A dermoscopic view of a skin lesion, a male subject in their 70s.
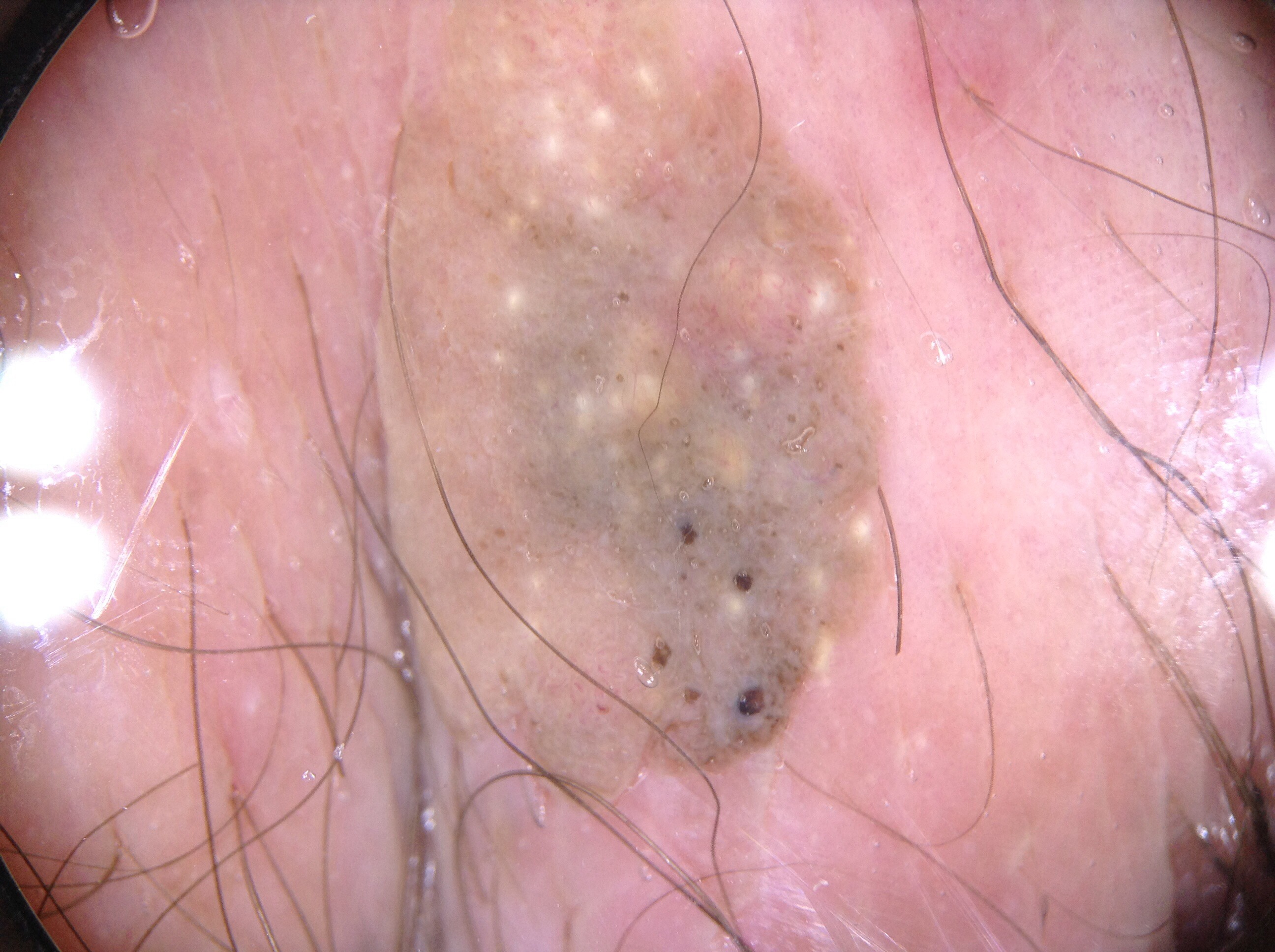Findings:
A prominent lesion filling much of the field. Dermoscopic examination shows milia-like cysts, with no streaks, pigment network, or negative network. In (x1, y1, x2, y2) order, the visible lesion spans bbox=[365, 2, 909, 812].
Conclusion:
Clinically diagnosed as a seborrheic keratosis.